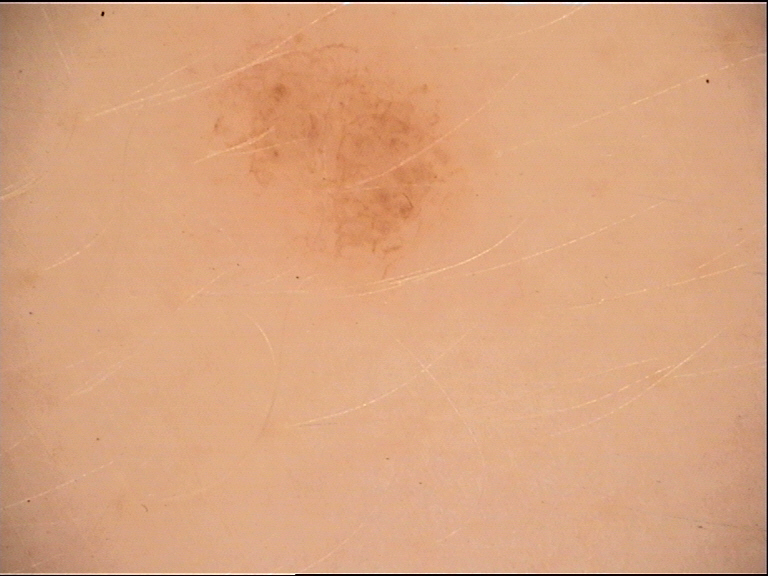A dermoscopic image of a skin lesion. Classified as a banal lesion — a junctional nevus.